This is a close-up image, the subject is female, located on the back of the hand.
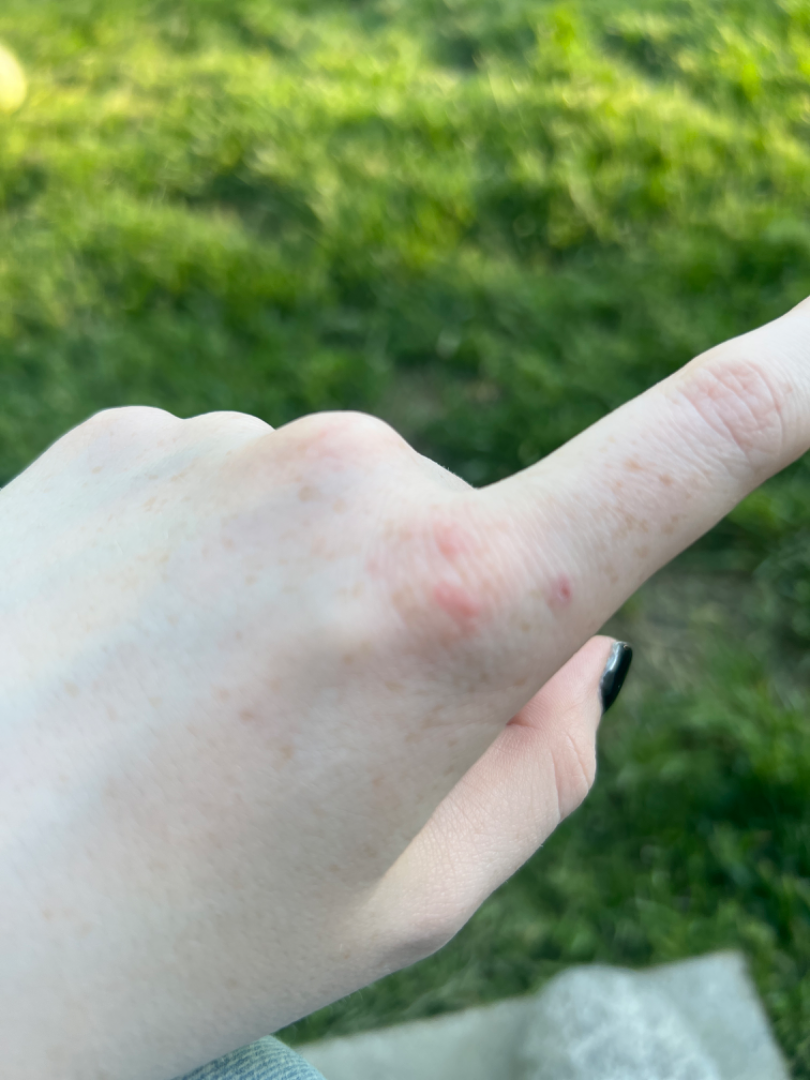| feature | finding |
|---|---|
| clinical impression | Allergic Contact Dermatitis (favored); Insect Bite (considered); Acute dermatitis, NOS (unlikely); Folliculitis (unlikely); Eczema (unlikely) |